A dermoscopic image of a skin lesion.
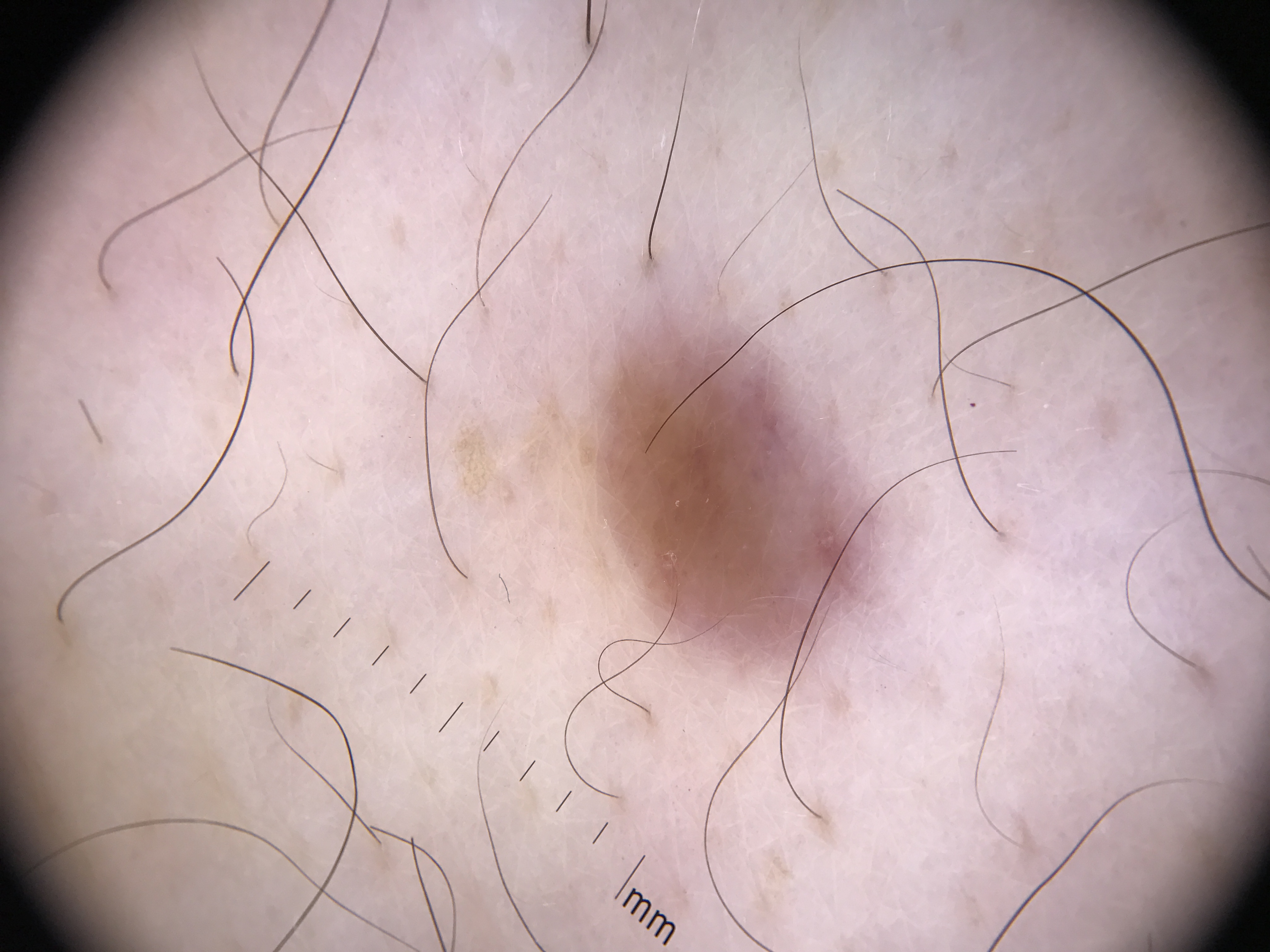Impression:
Consistent with a banal lesion — a junctional nevus.